A skin lesion imaged with a dermatoscope.
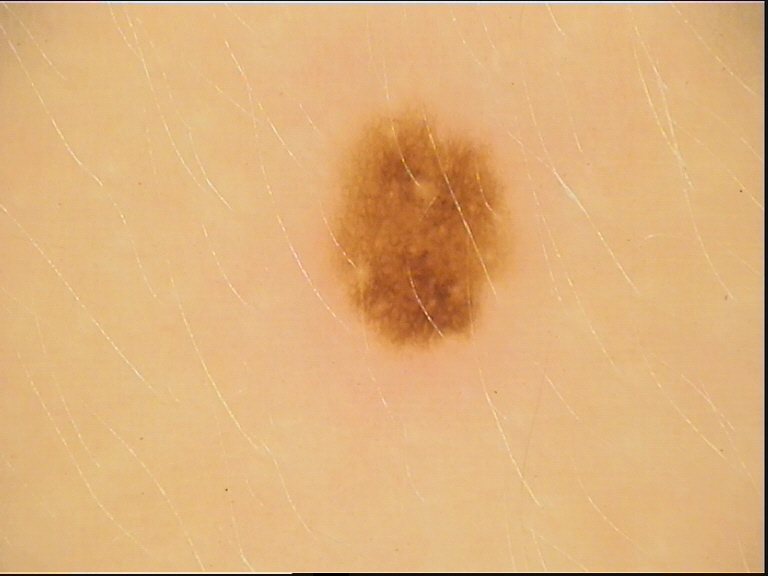<case>
  <diagnosis>
    <name>dysplastic junctional nevus</name>
    <code>jd</code>
    <malignancy>benign</malignancy>
    <super_class>melanocytic</super_class>
    <confirmation>expert consensus</confirmation>
  </diagnosis>
</case>